A dermatoscopic image of a skin lesion.
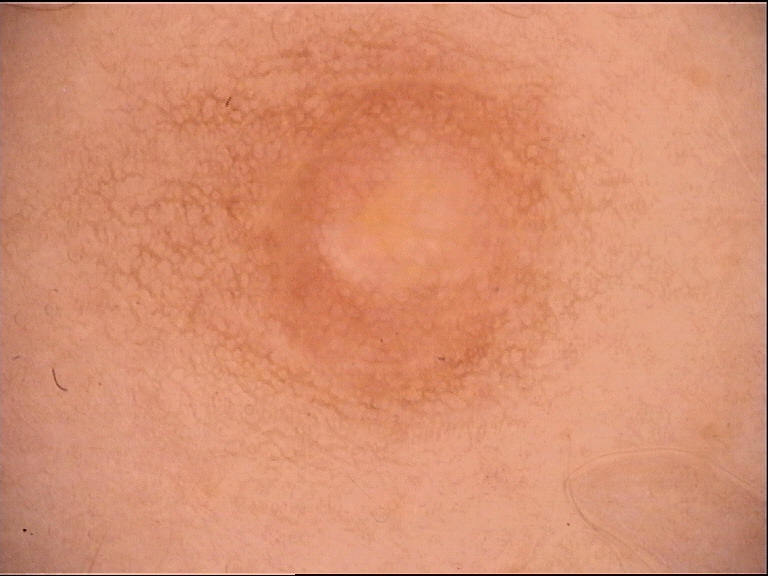label: dermal nevus (expert consensus)